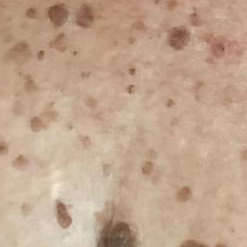A female subject in their late 50s.
A smartphone photograph of a skin lesion.
The chart records prior malignancy (patient or family), prior skin cancer (patient or family), and no alcohol use.
The lesion is located on the chest.
The lesion is roughly 17 by 15 mm.
The patient reports that the lesion has grown and is elevated.
Consistent with a benign lesion — a seborrheic keratosis.